A patient in their 60s: 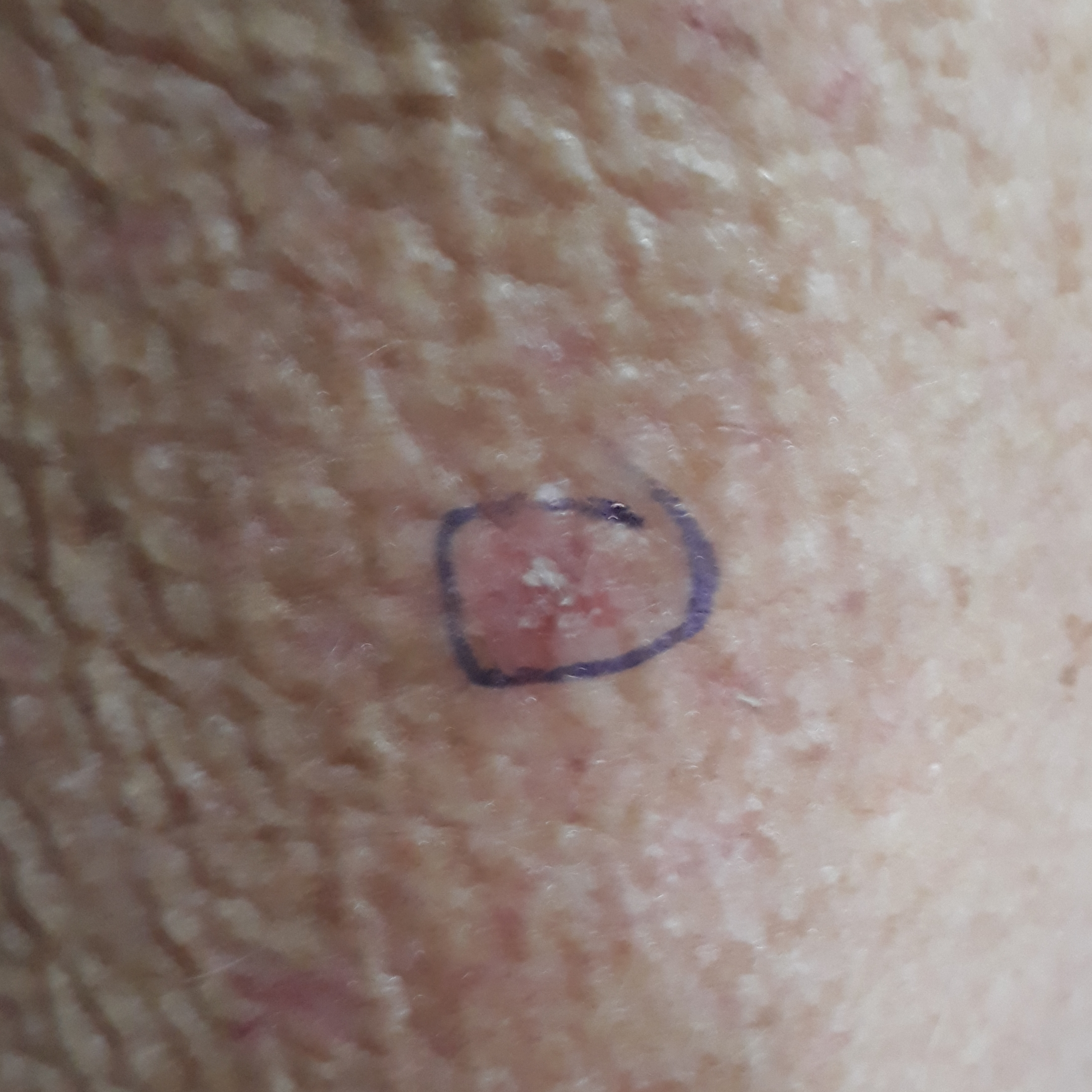Case summary: The lesion involves an arm. Per patient report, the lesion has grown, itches, and has bled. Impression: Clinically diagnosed as a premalignant lesion — an actinic keratosis.